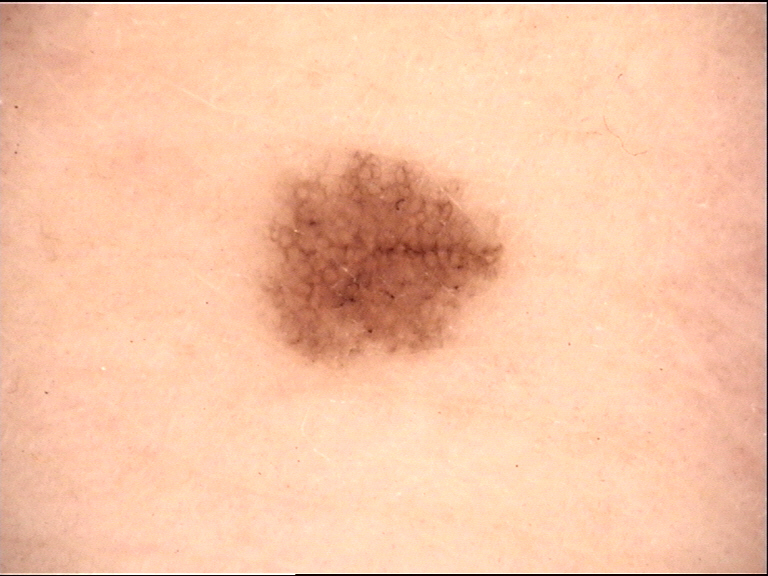assessment: acral dysplastic junctional nevus (expert consensus).